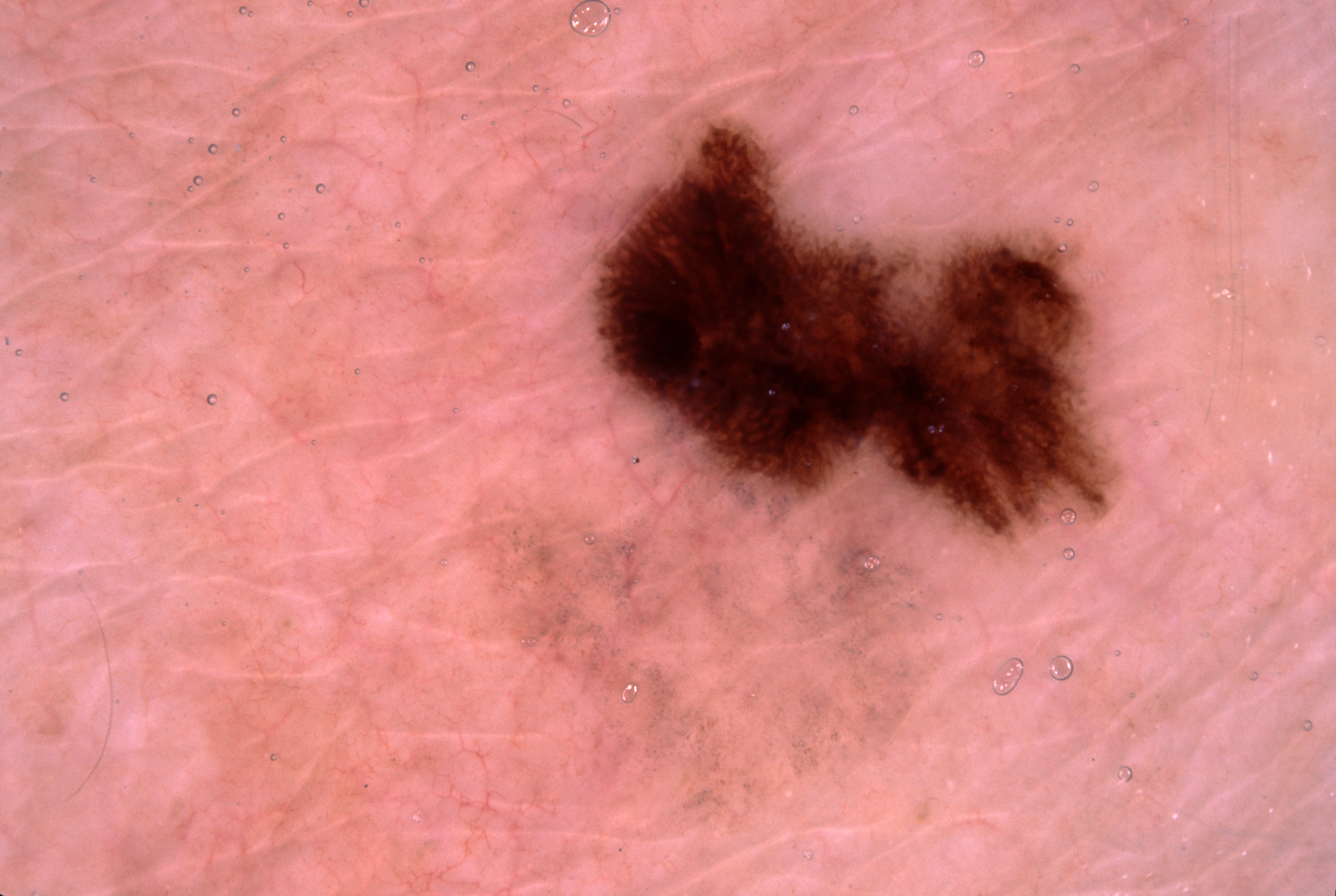<lesion>
<image>
  <modality>dermoscopy</modality>
</image>
<lesion_location>
  <bbox_xyxy>586, 119, 1114, 542</bbox_xyxy>
</lesion_location>
<lesion_extent>
  <approx_field_fraction_pct>11</approx_field_fraction_pct>
</lesion_extent>
<dermoscopic_features>
  <present>pigment network</present>
  <absent>negative network, streaks, milia-like cysts</absent>
</dermoscopic_features>
<diagnosis>
  <name>melanoma</name>
  <malignancy>malignant</malignancy>
  <lineage>melanocytic</lineage>
  <provenance>histopathology</provenance>
</diagnosis>
</lesion>